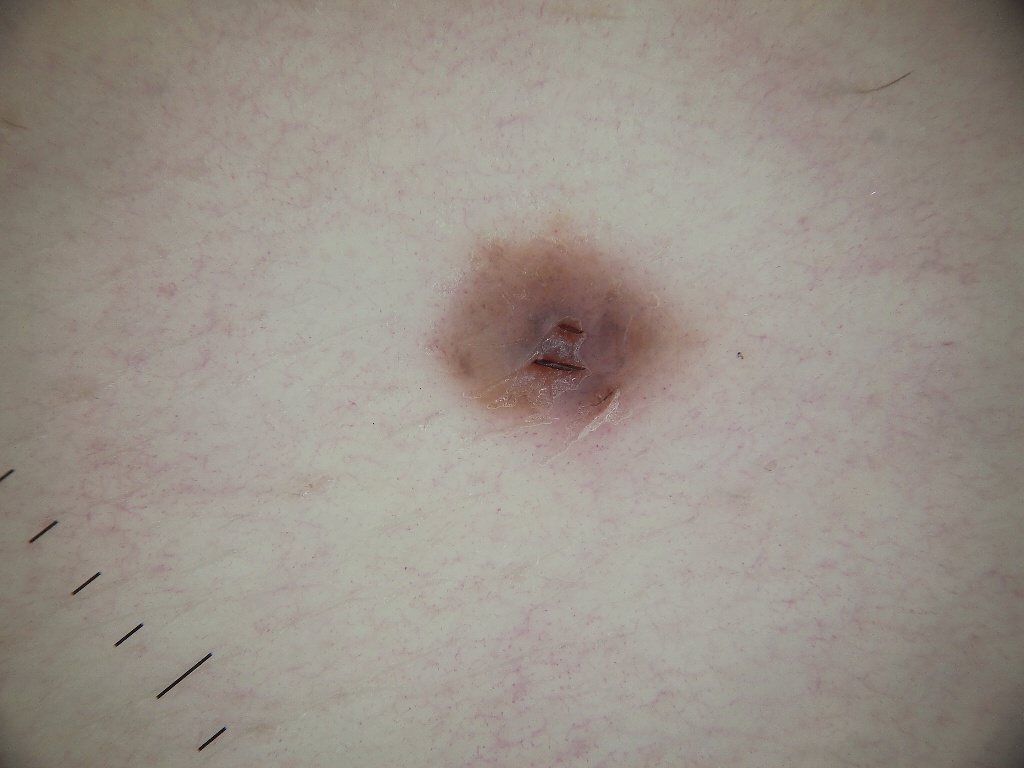The patient is a female aged around 55.
This is a dermoscopic photograph of a skin lesion.
The dermoscopic pattern shows no negative network, streaks, milia-like cysts, globules, or pigment network.
With coordinates (x1, y1, x2, y2), the lesion's extent is <bbox>432, 229, 697, 432</bbox>.
Diagnosed as a melanocytic nevus, a benign lesion.